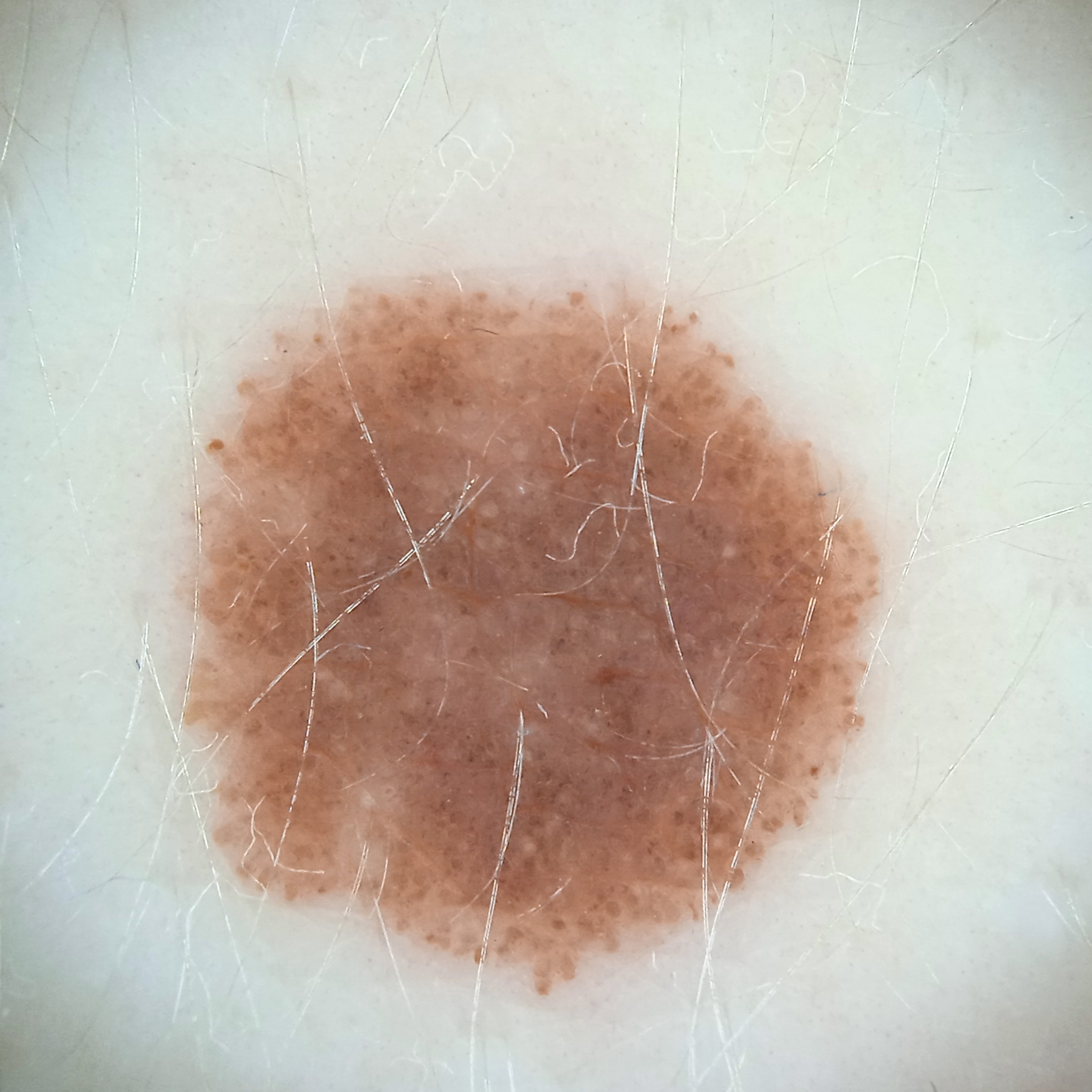– imaging: dermatoscopic image
– referral: research study (no referral diagnosis)
– sun reaction: skin reddens with sun exposure
– subject: female, 26 years of age
– nevus count: numerous melanocytic nevi
– risk factors: a history of sunbed use
– body site: the back
– diameter: 9.1 mm
– diagnostic label: melanocytic nevus (dermatologist consensus)